The affected area is the leg · an image taken at a distance · reported lesion symptoms include burning, enlargement, bothersome appearance, pain and itching · the patient is a female aged 18–29 · the patient notes the condition has been present for one to four weeks · the patient considered this a rash — 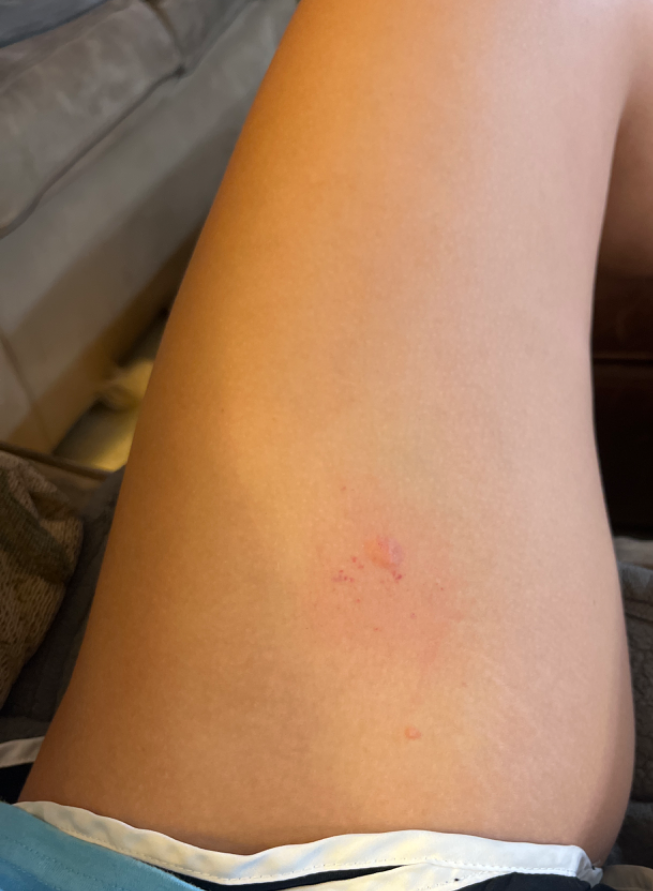Case summary:
– differential — Verruca vulgaris (0.50); SCC/SCCIS (0.50)